A close-up photograph; the affected area is the leg.
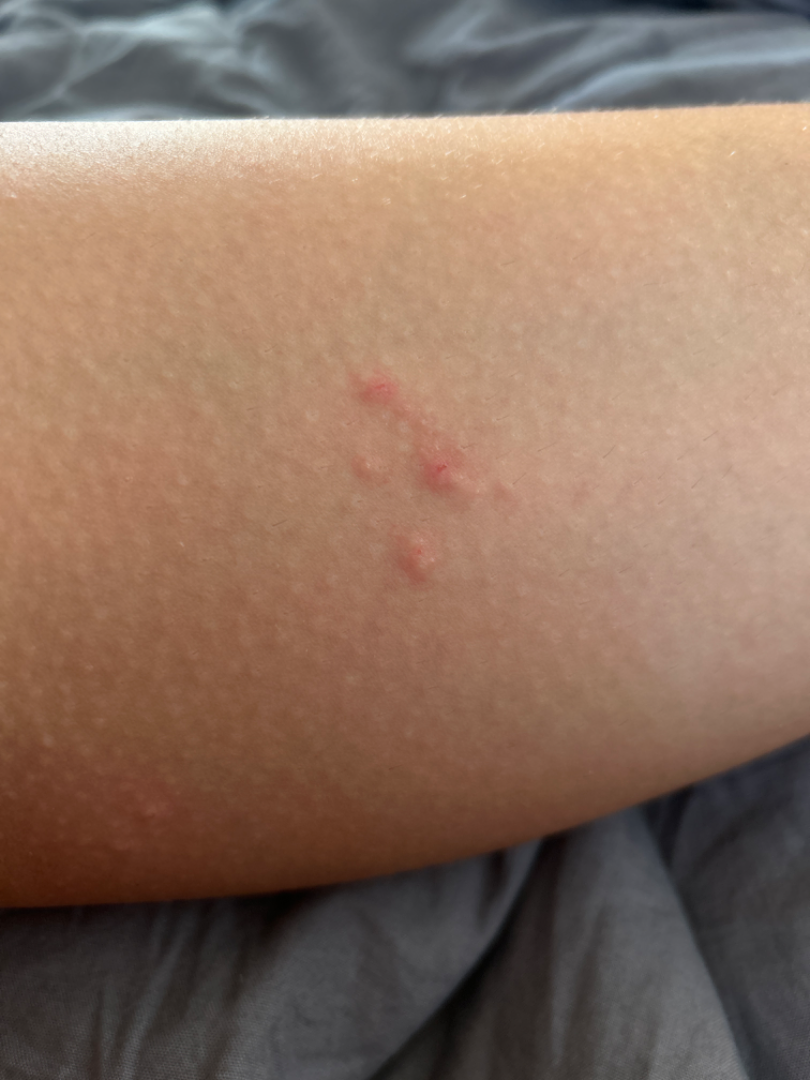clinical impression: Insect Bite (considered); Allergic Contact Dermatitis (considered); Herpes Simplex (considered).